The front of the torso, arm, back of the torso and leg are involved. The contributor is female. This image was taken at an angle: 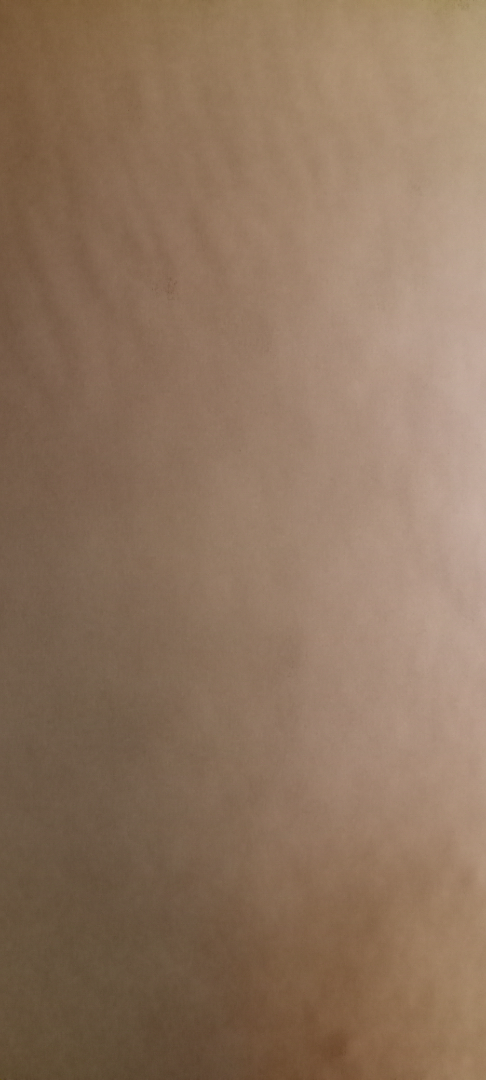The reviewing dermatologist was unable to assign a differential diagnosis from the image.